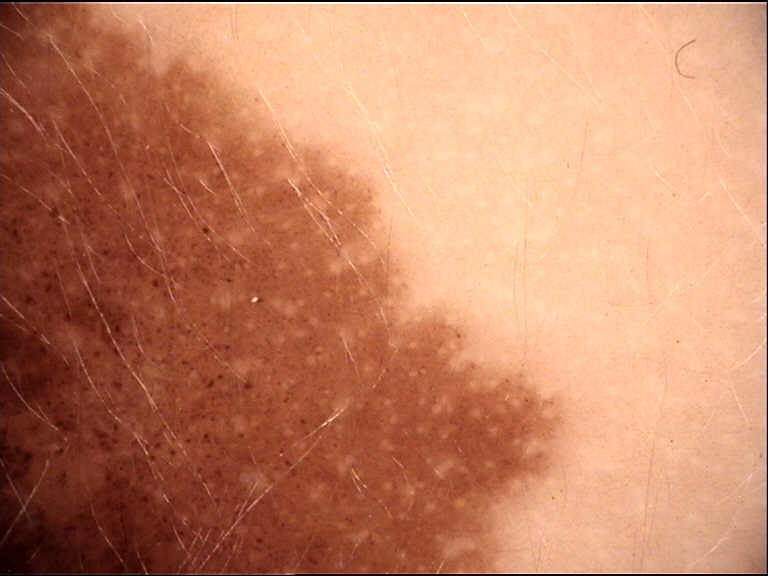Findings:
• image type: dermoscopy
• category: banal
• assessment: congenital junctional nevus (expert consensus)